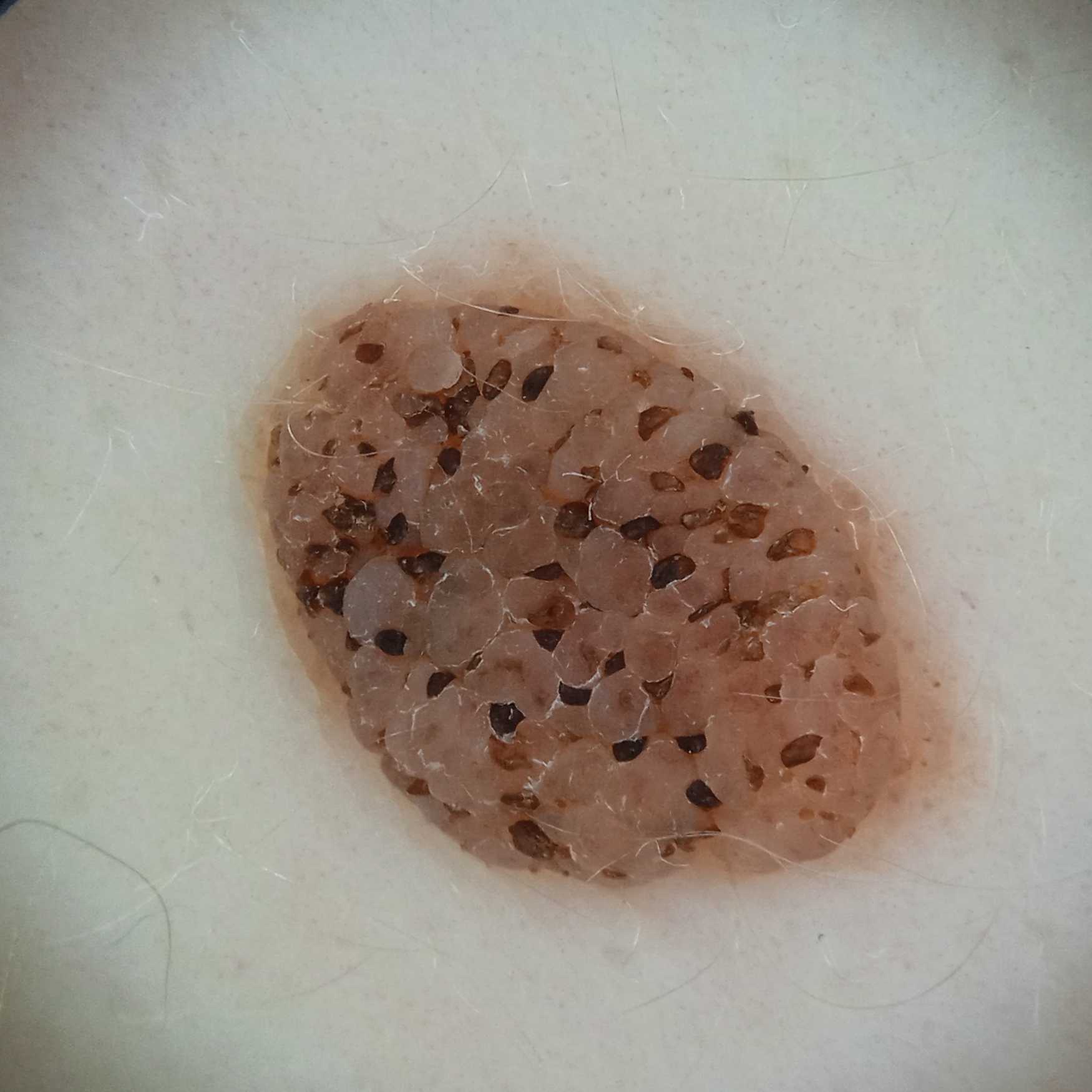referral context: research study (no referral diagnosis), diameter: 8.4 mm, diagnosis: seborrheic keratosis (dermatologist consensus).